An image taken at a distance · the patient indicates bothersome appearance, enlargement, itching and darkening · the patient indicates the condition has been present for one to three months · the patient indicates the lesion is raised or bumpy · the patient described the issue as a rash · the affected area is the leg, head or neck, front of the torso and back of the torso: 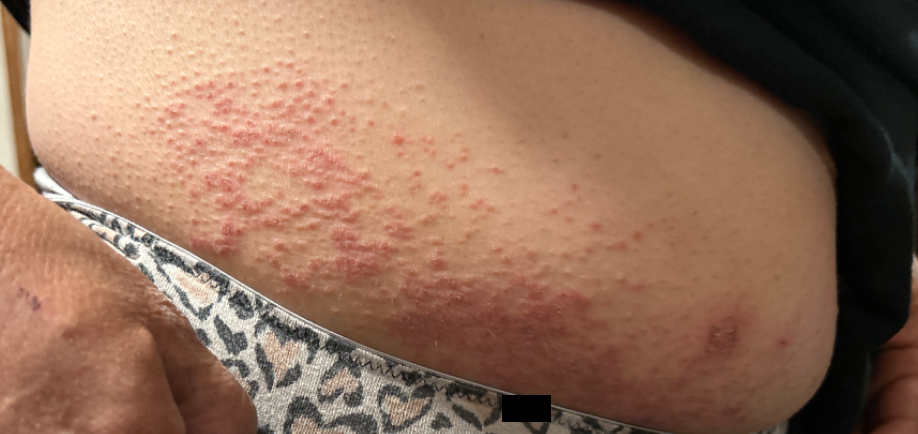Findings:
Eczema (weight 1.00).